The patient reported no systemic symptoms, the contributor reports the condition has been present for less than one week, the top or side of the foot is involved, the photo was captured at a distance, self-categorized by the patient as a rash, the contributor is a male aged 18–29.
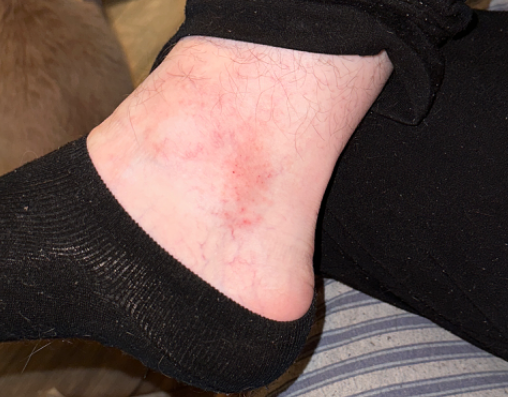Findings:
Eczema (primary); Irritant Contact Dermatitis (possible); Stasis Dermatitis (lower probability); Allergic Contact Dermatitis (lower probability).